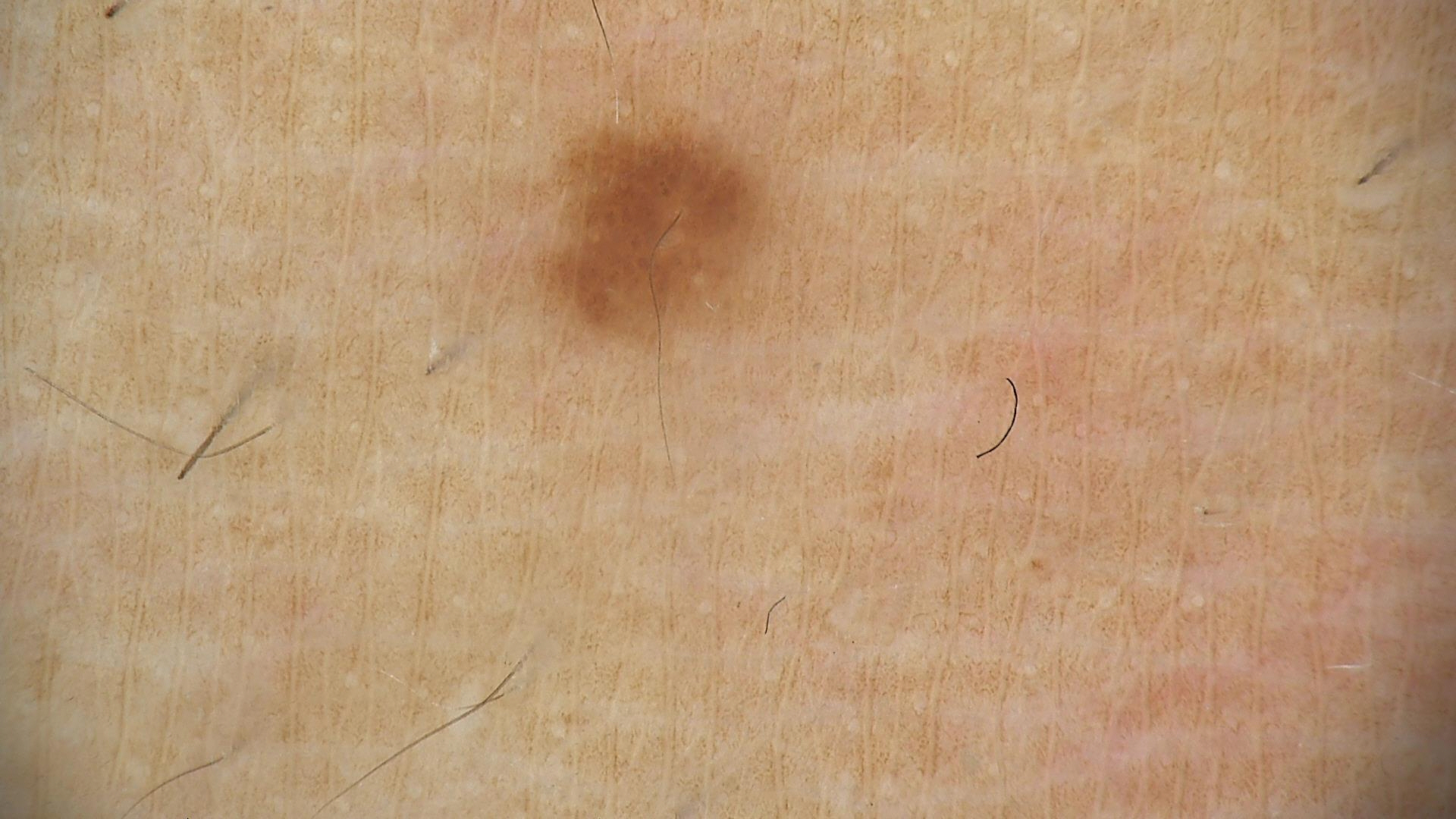assessment = dysplastic junctional nevus (expert consensus).